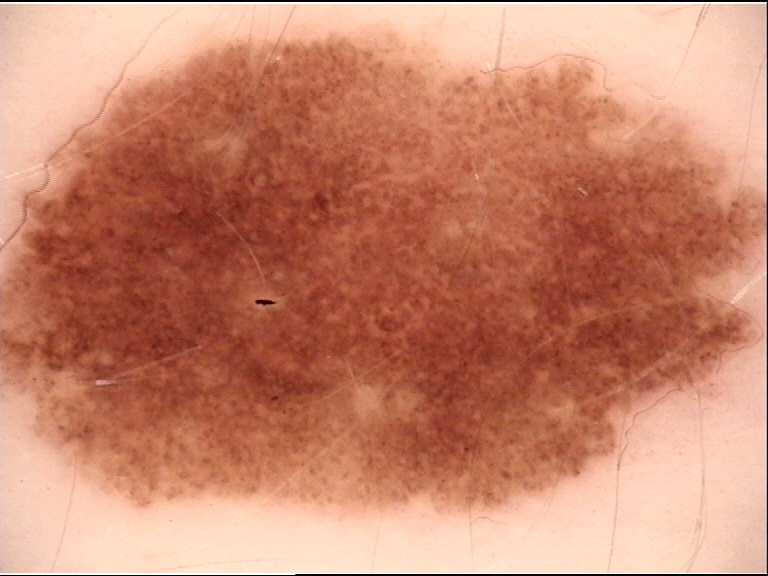diagnostic label = dysplastic junctional nevus (expert consensus).